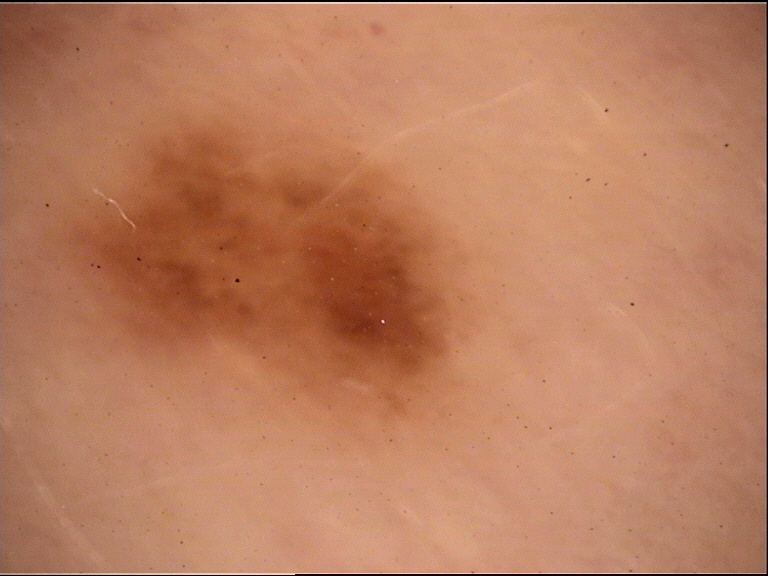modality: dermoscopy
class: dysplastic junctional nevus (expert consensus)